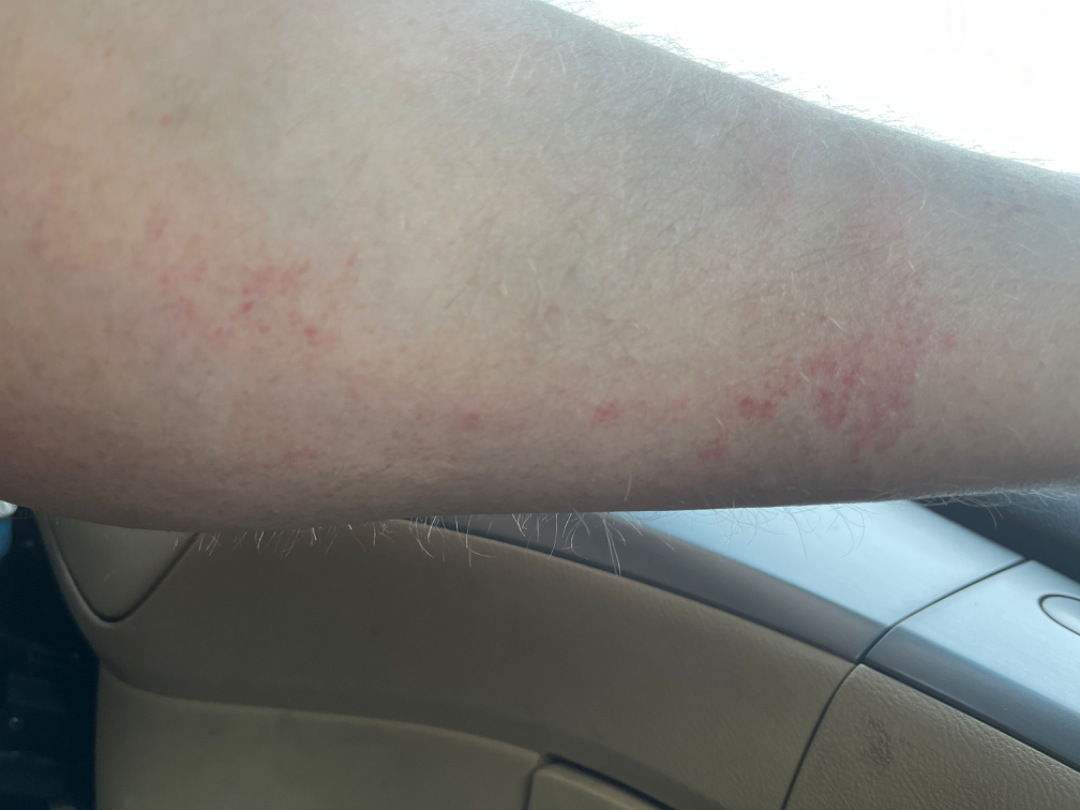assessment: Traumatic petechiae, Allergic Contact Dermatitis and Leukocytoclastic Vasculitis were each considered, in no particular order.